A dermoscopic close-up of a skin lesion — 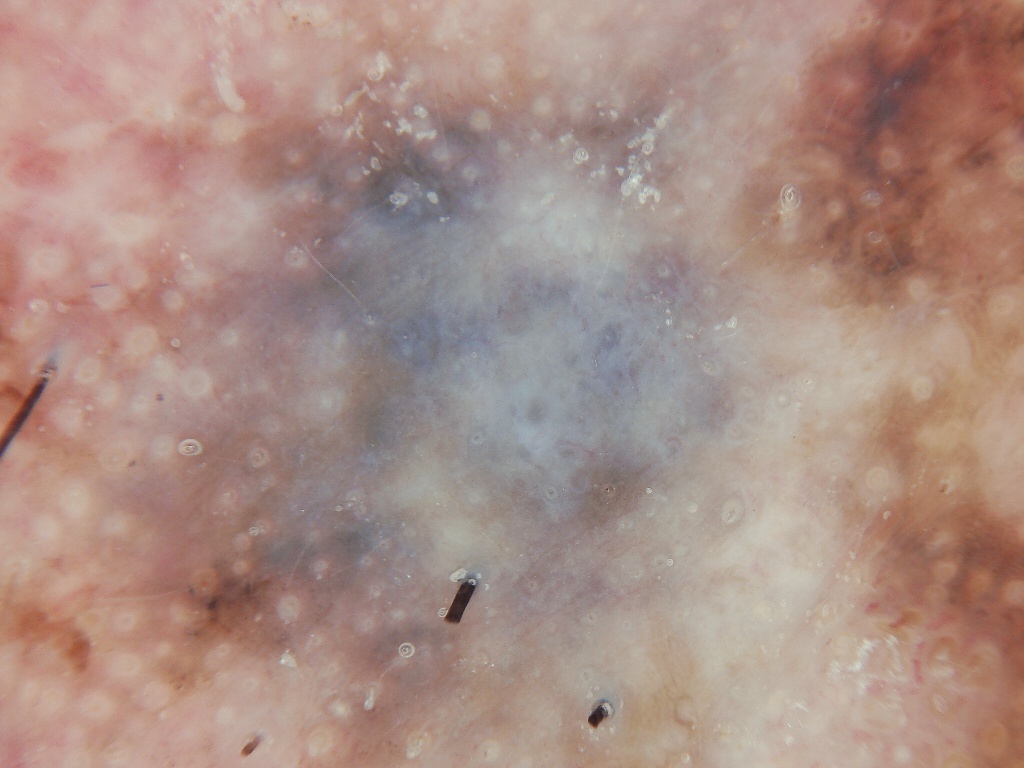lesion location=reaches across the whole image | diagnostic label=a malignancy.